Dermoscopy of a skin lesion.
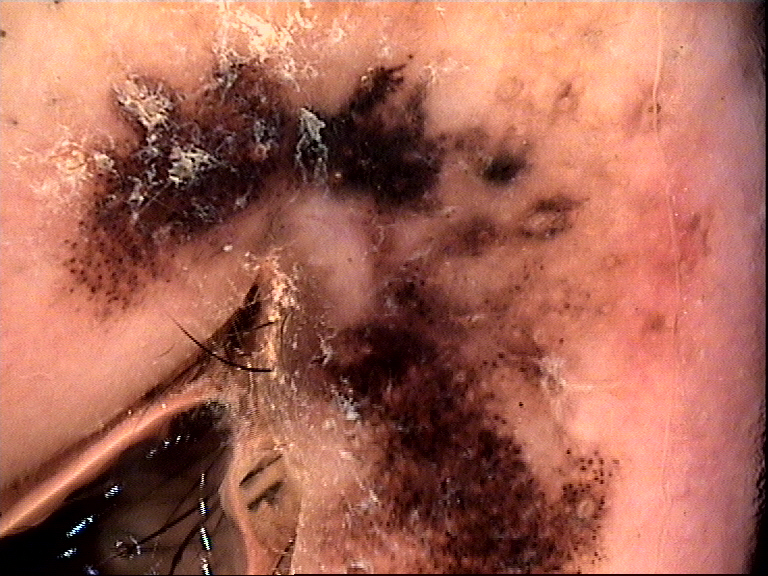Histopathology confirmed a melanoma.